A clinical photograph showing a skin lesion · collected as part of a research study, without a referral diagnosis · a female patient 92 years old · the patient says their skin tans without first burning: 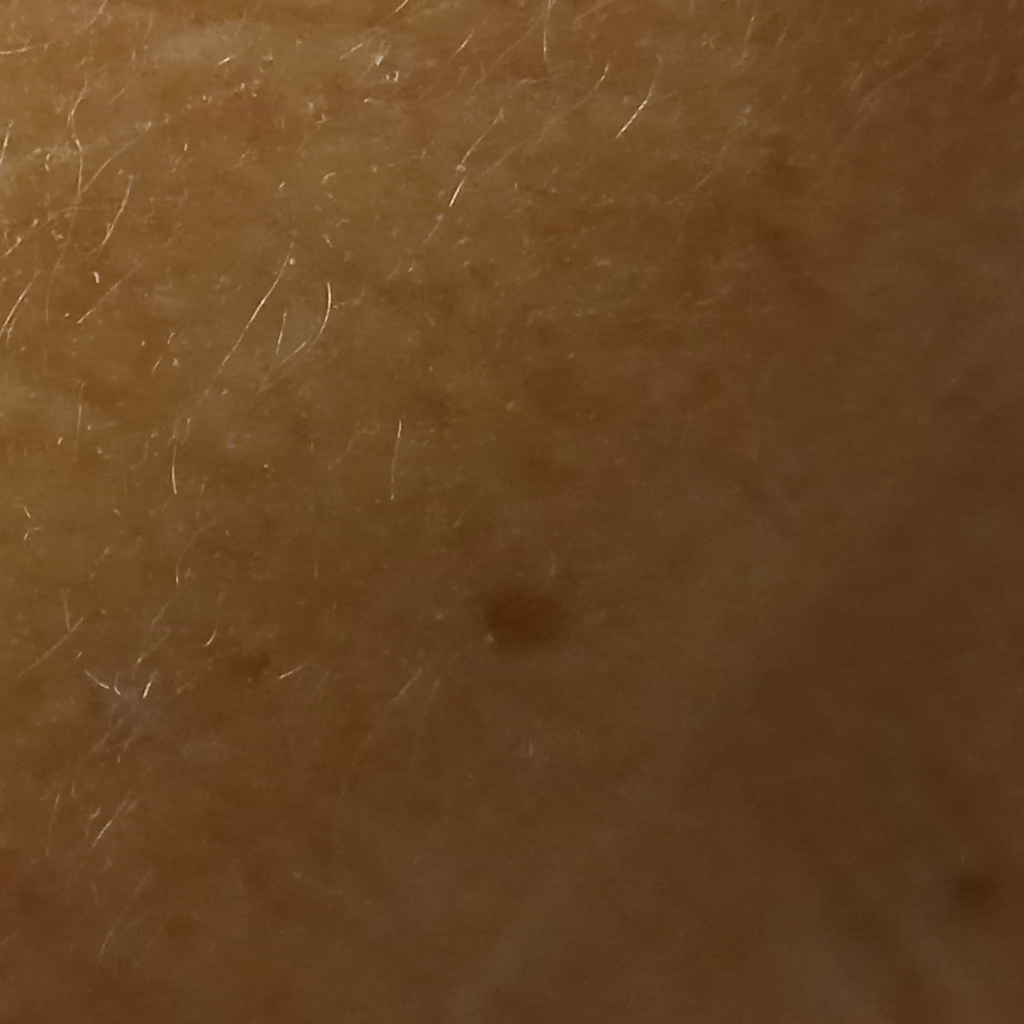| feature | finding |
|---|---|
| anatomic site | the face |
| size | 2.9 mm |
| assessment | melanocytic nevus (dermatologist consensus) |